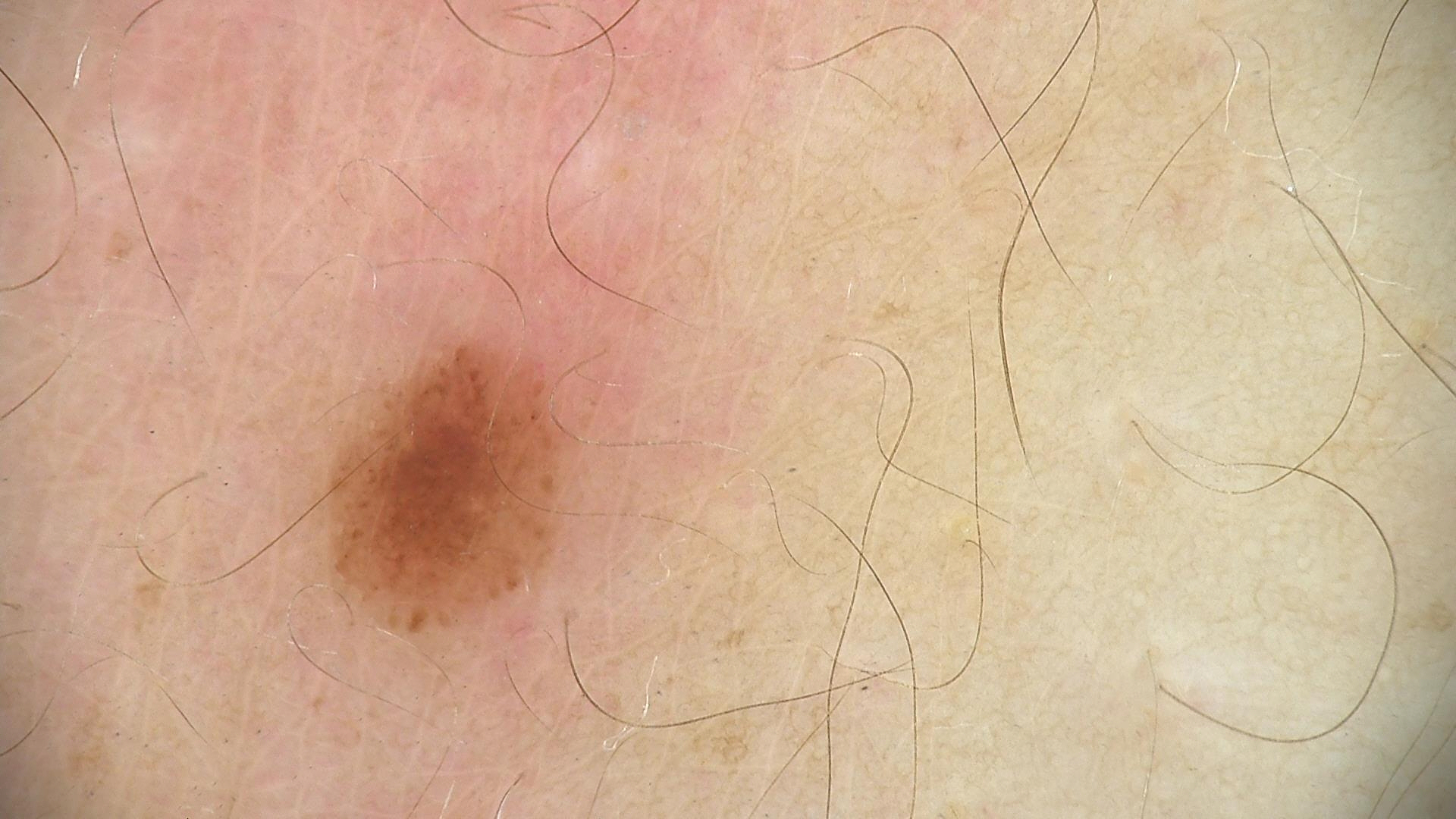A dermoscopic close-up of a skin lesion. Diagnosed as a dysplastic junctional nevus.